A close-up photograph. Female subject, age 18–29: 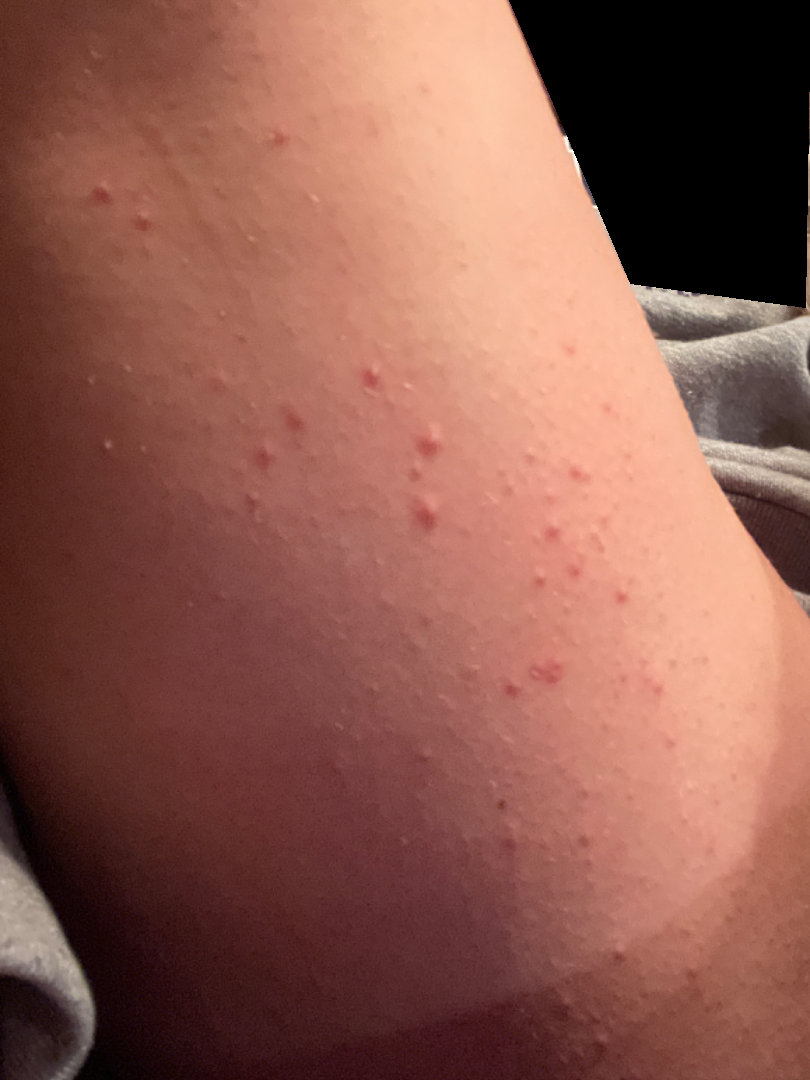On remote dermatologist review, the primary impression is Folliculitis; also consider Keratosis pilaris; a more distant consideration is Eczema.